The patient indicates the condition has been present for about one day, the subject is female, the photograph is a close-up of the affected area, the lesion is described as flat, the patient considered this skin that appeared healthy to them, the patient did not report lesion symptoms, the lesion involves the leg: 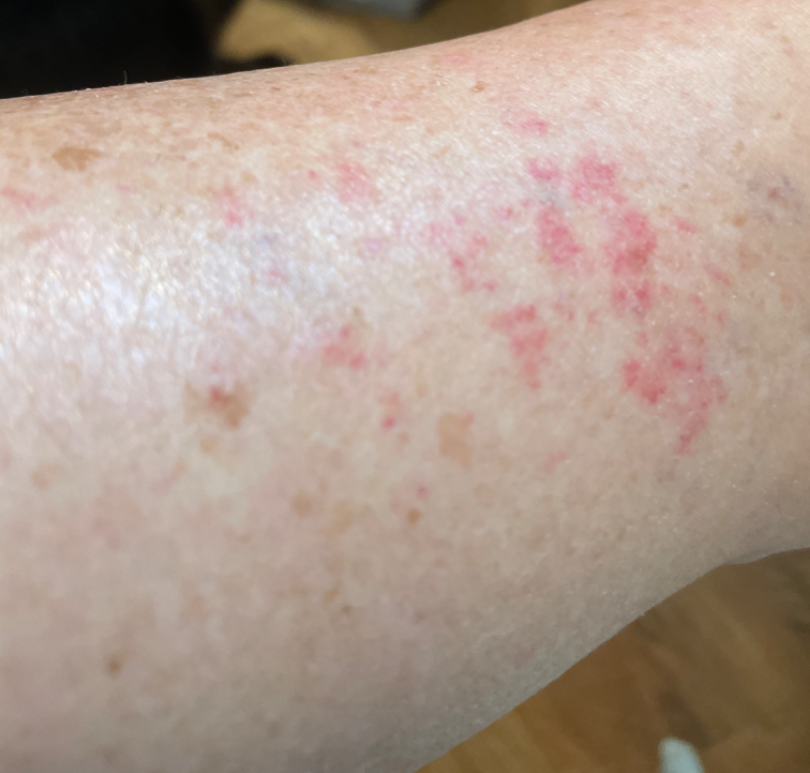<report>
<differential>
  <tied_lead>Allergic Contact Dermatitis, Stasis Dermatitis, Eczema, Contact dermatitis</tied_lead>
</differential>
</report>